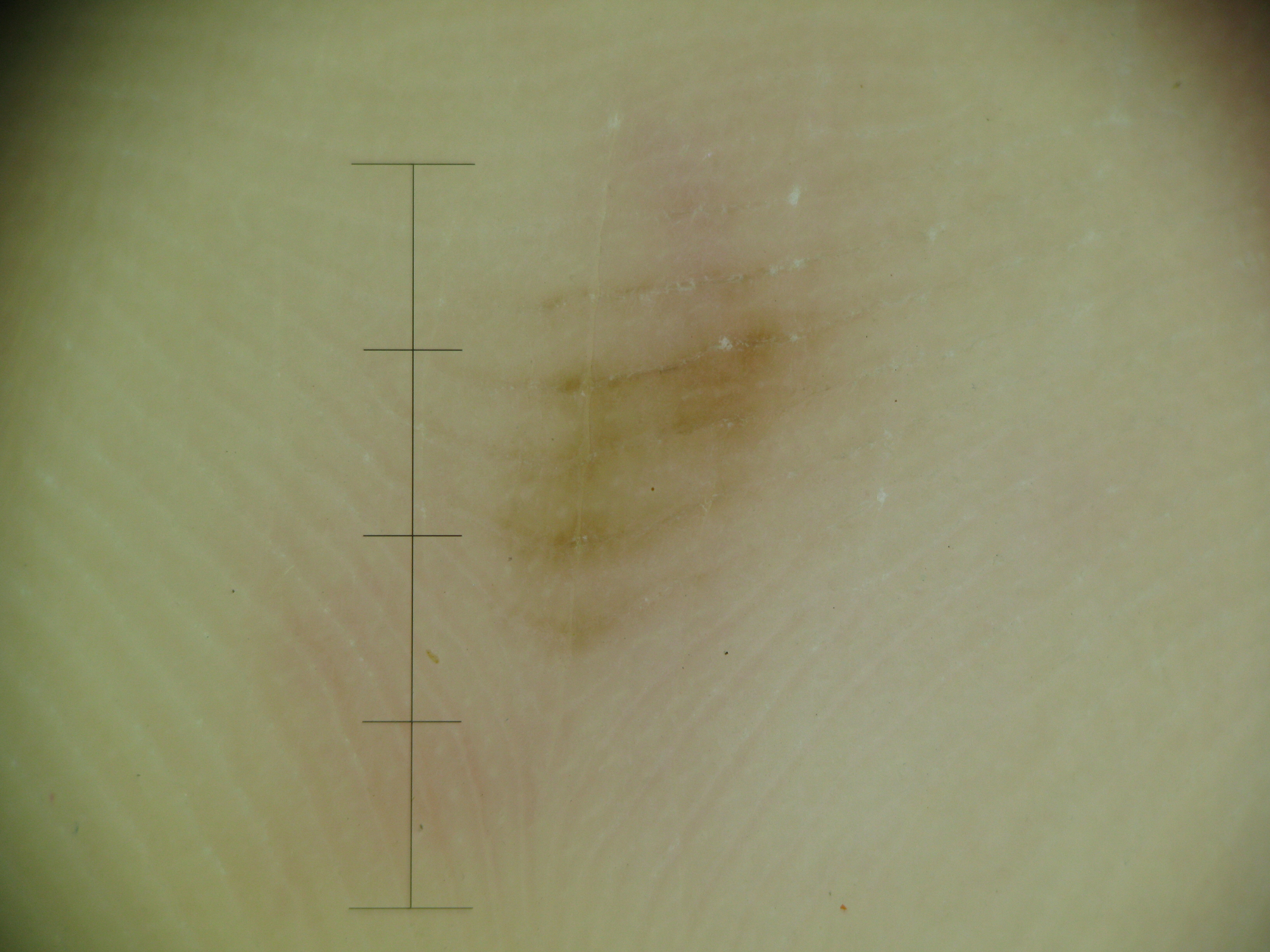{"image": "dermoscopy", "lesion_type": {"main_class": "banal", "pattern": "junctional"}, "diagnosis": {"name": "acral junctional nevus", "code": "ajb", "malignancy": "benign", "super_class": "melanocytic", "confirmation": "expert consensus"}}